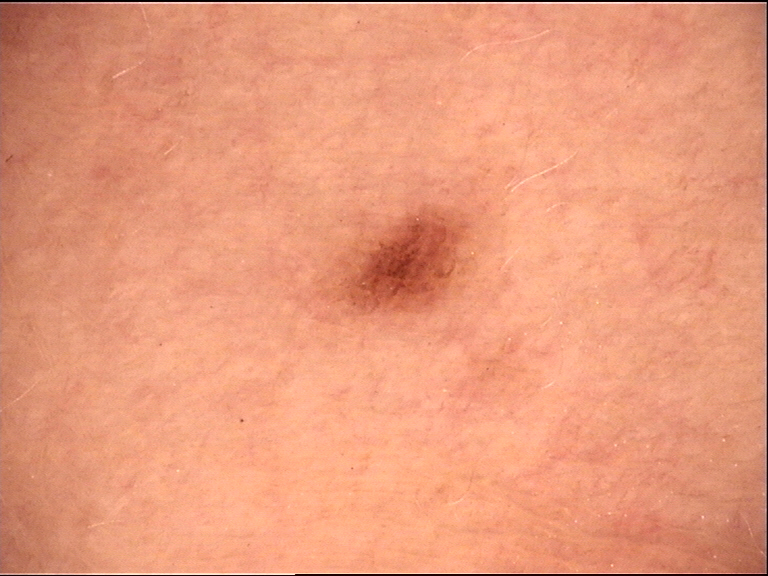– diagnosis · dysplastic junctional nevus (expert consensus)